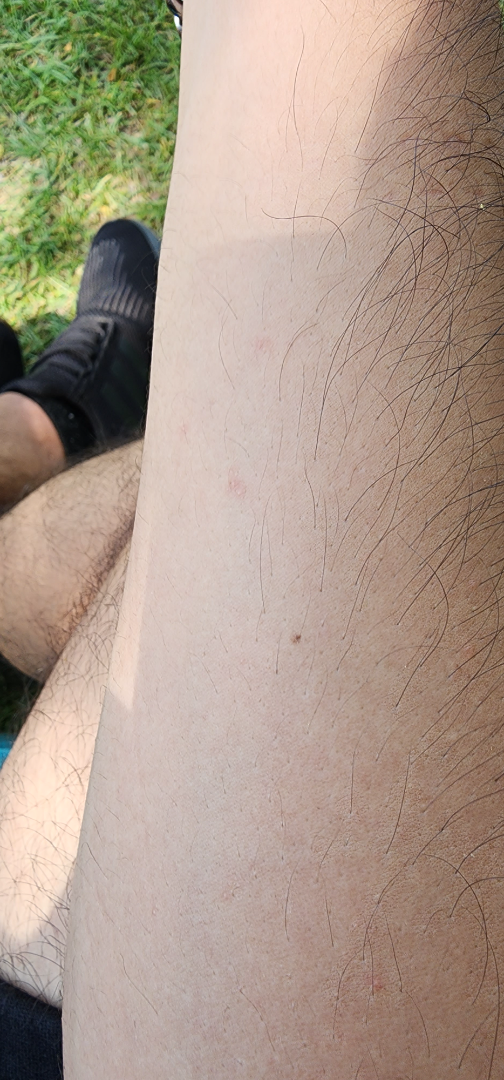Q: What is the framing?
A: at an angle
Q: What is the affected area?
A: arm
Q: Patient demographics?
A: male, age 30–39
Q: What conditions are considered?
A: three independent reviewers: Insect Bite and Folliculitis were considered with similar weight